Associated systemic symptoms include fatigue and joint pain; skin tone: non-clinician graders estimated Monk skin tone scale 2; the contributor reports darkening, pain, itching and burning; an image taken at an angle; reported duration is three to twelve months; the back of the hand is involved: 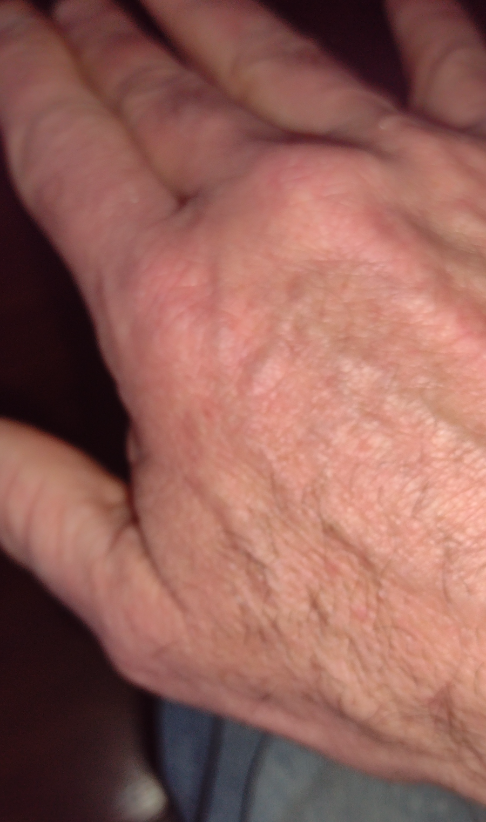No discernible skin pathology was identified on dermatologist review.